No relevant systemic symptoms. Texture is reported as raised or bumpy. The patient reports bothersome appearance. This is a close-up image. The contributor is 50–59, female. The condition has been present for about one day. Located on the palm: 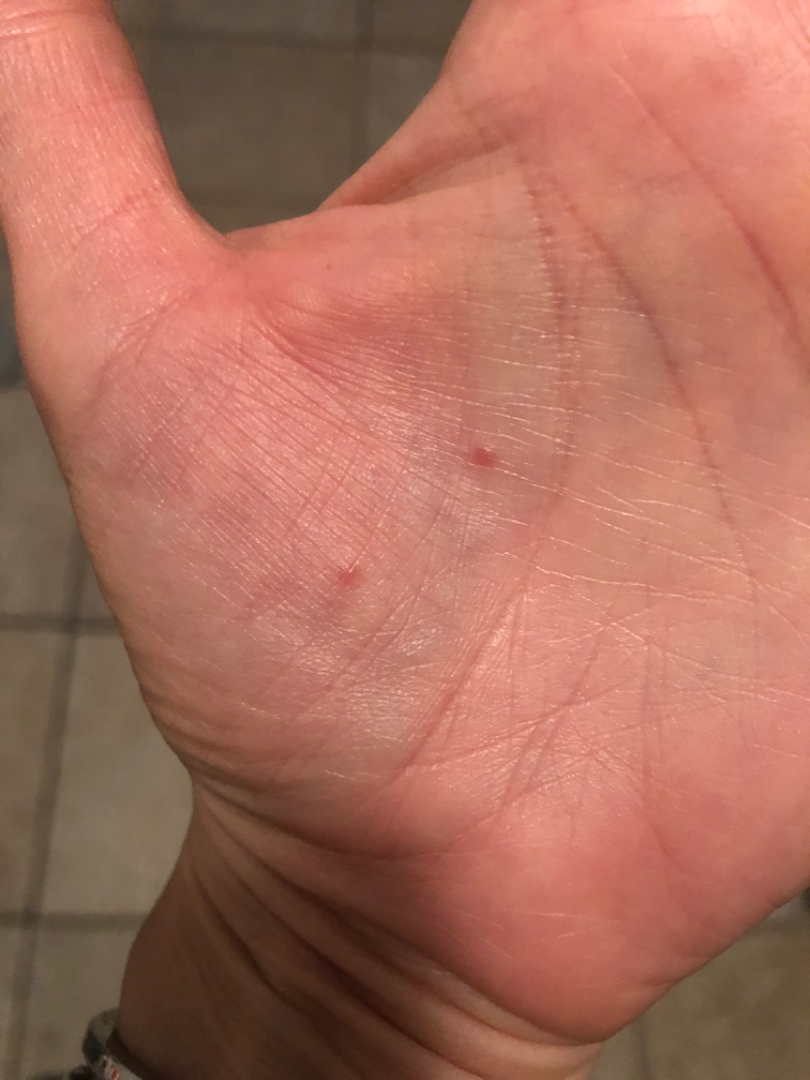{
  "differential": "Eczema"
}